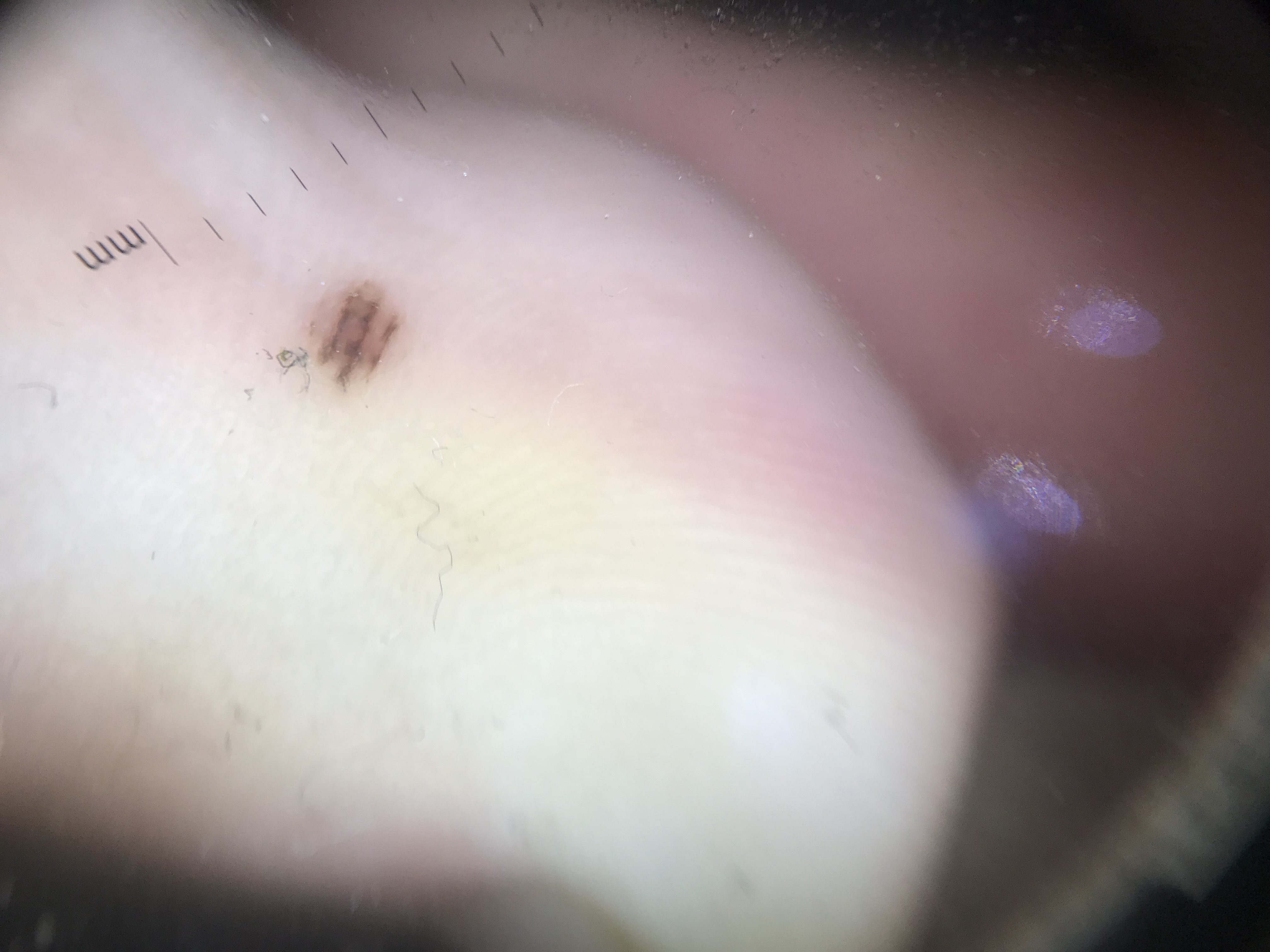| feature | finding |
|---|---|
| imaging | dermoscopy |
| label | acral dysplastic junctional nevus (expert consensus) |